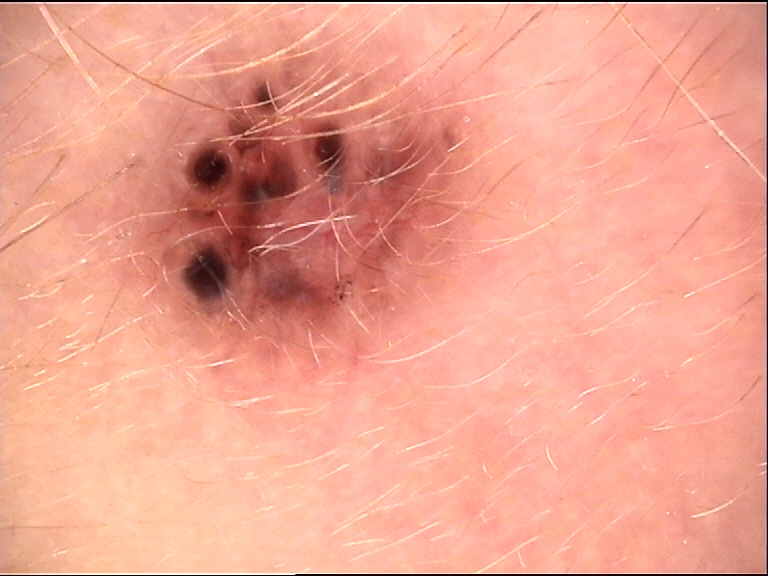Case:
A dermoscopic photograph of a skin lesion.
Conclusion:
Confirmed on histopathology as a keratinocytic, malignant lesion — a basal cell carcinoma.